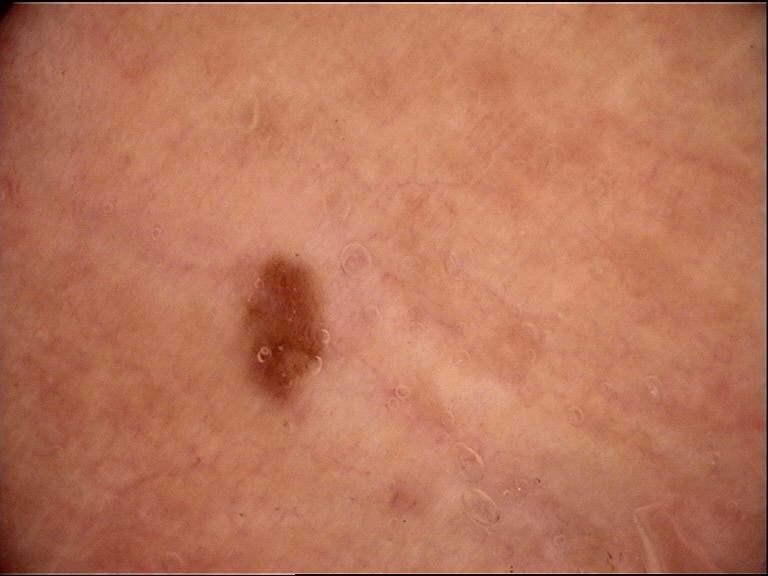Consistent with a benign lesion — a dysplastic junctional nevus.